Dermoscopy of a skin lesion.
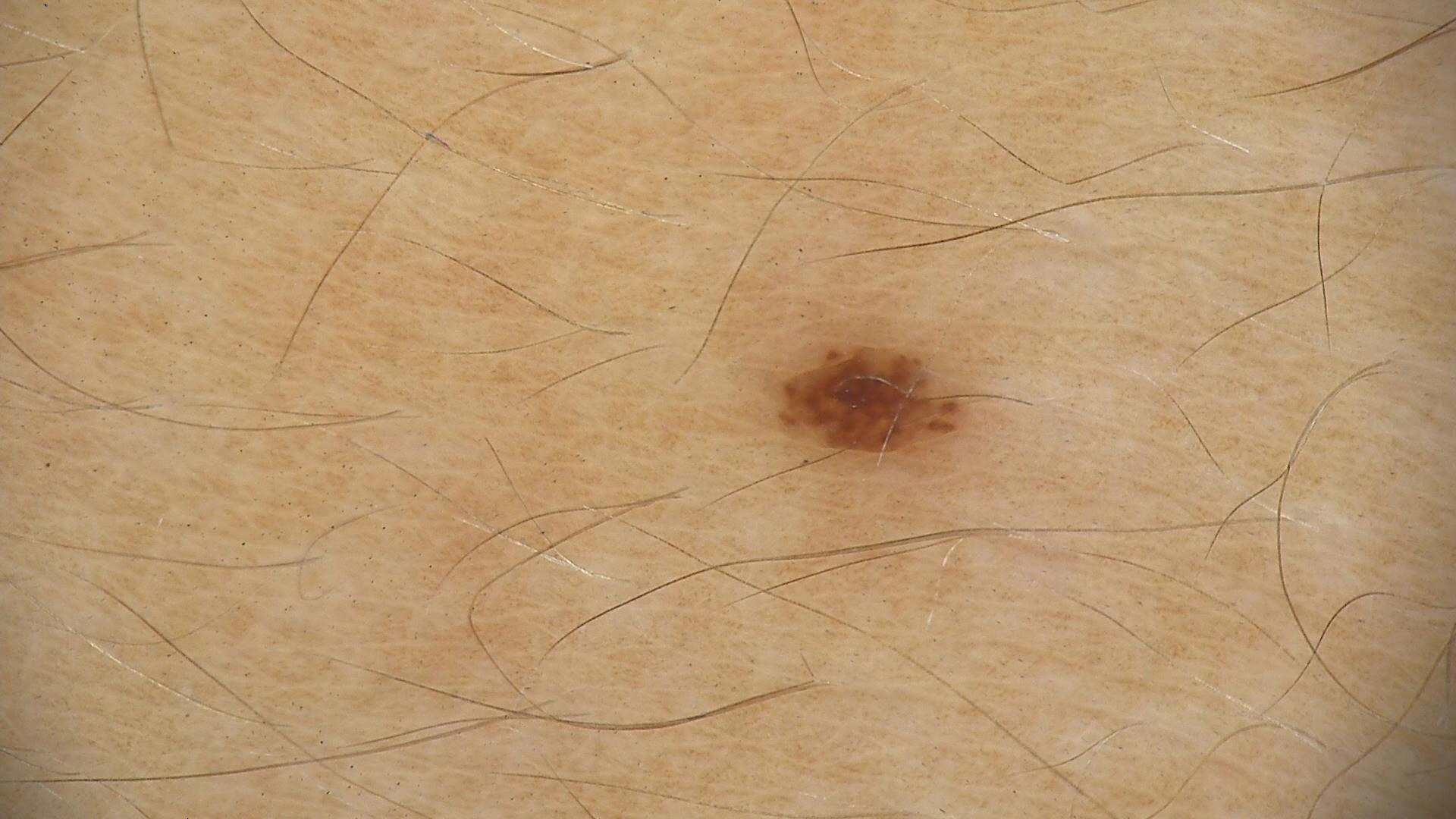Consistent with a benign lesion — a dysplastic junctional nevus.